The patient is 18–29, male; reported lesion symptoms include pain and itching; the palm and back of the hand are involved; no relevant systemic symptoms; reported duration is more than five years; the contributor notes the lesion is raised or bumpy; the photograph was taken at an angle: 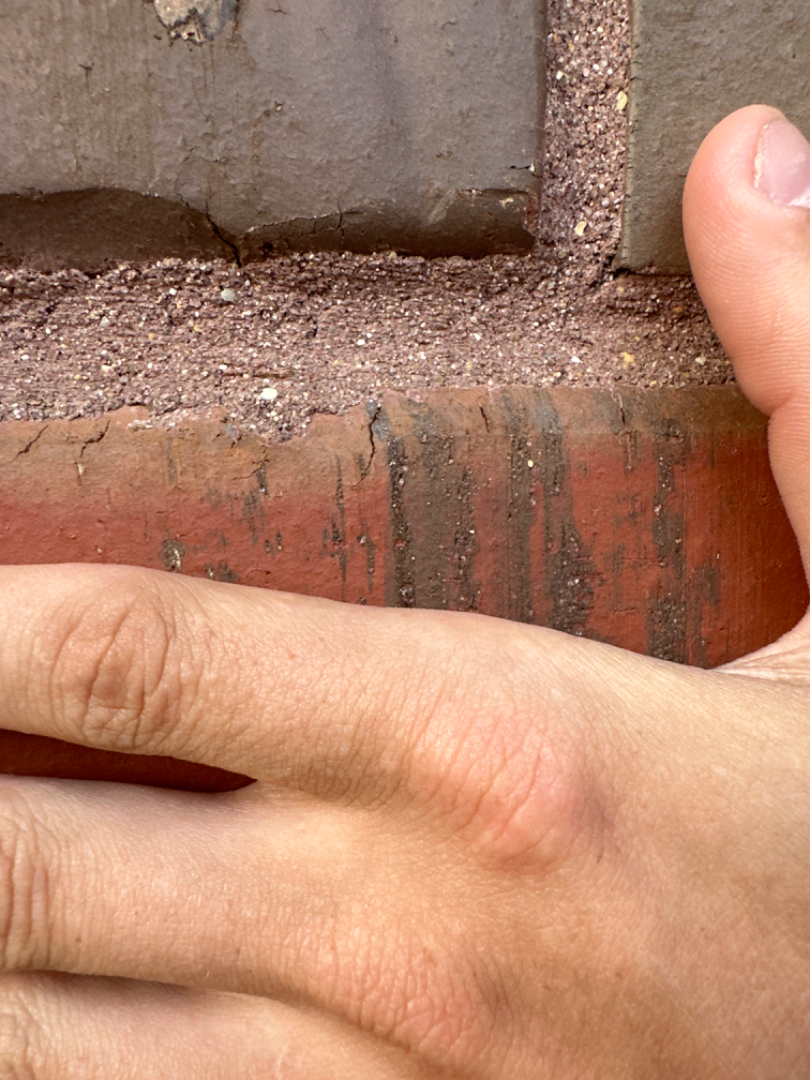The image was not sufficient for the reviewer to characterize the skin condition.